The photo was captured at a distance.
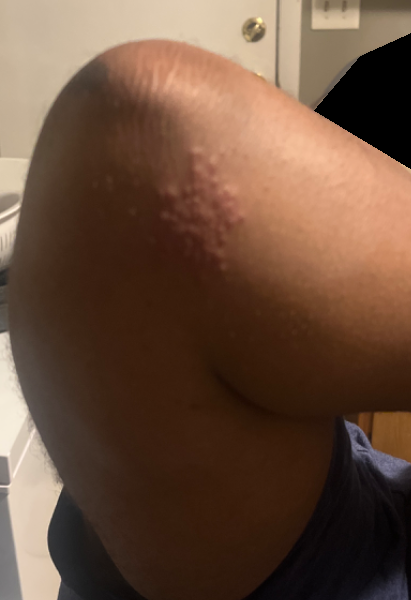* diagnostic considerations · Herpes Zoster (considered); Allergic Contact Dermatitis (considered); Herpes Simplex (considered)